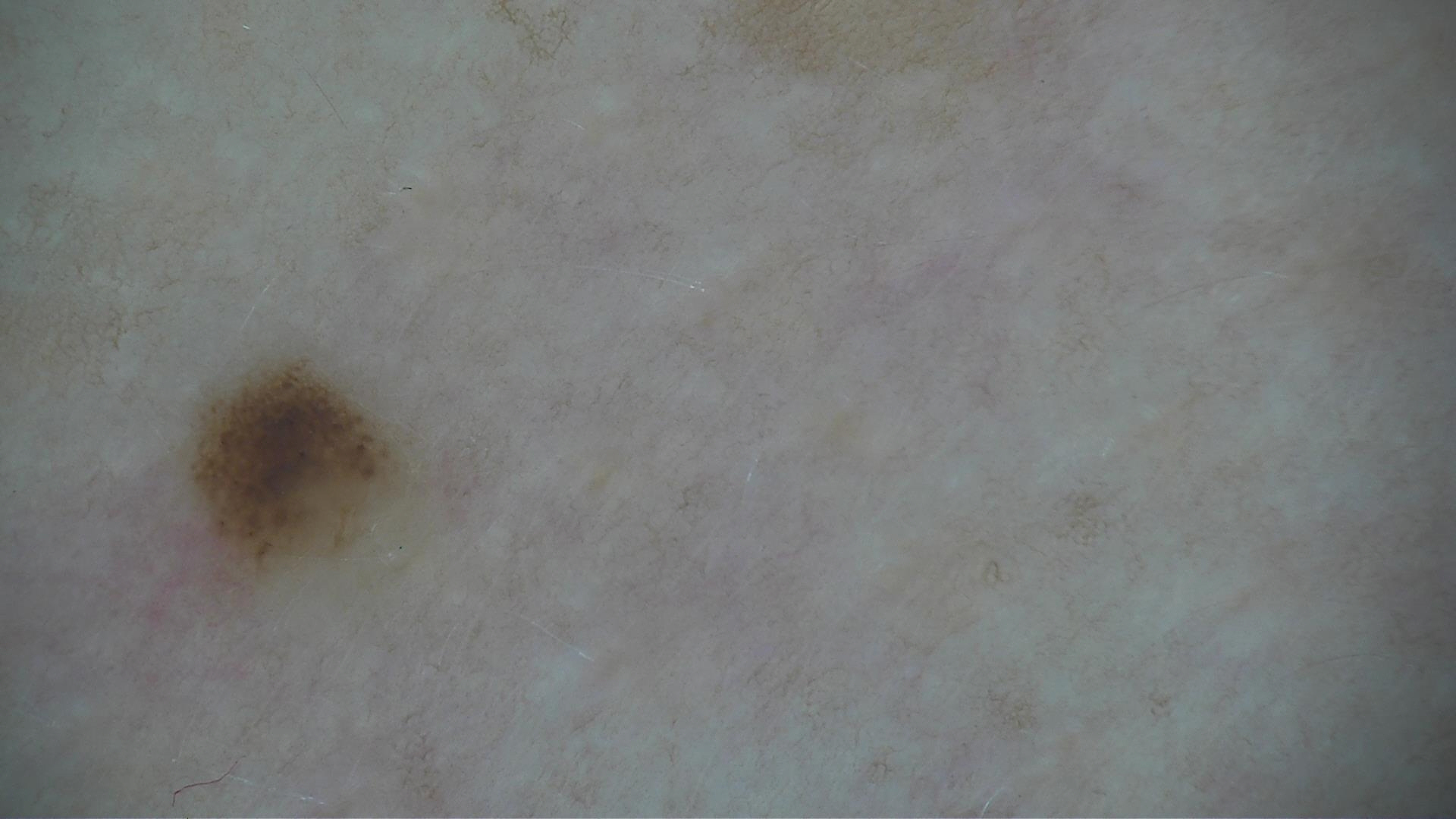modality: dermatoscopy, diagnosis: dysplastic junctional nevus (expert consensus).